A dermoscopic image of a skin lesion.
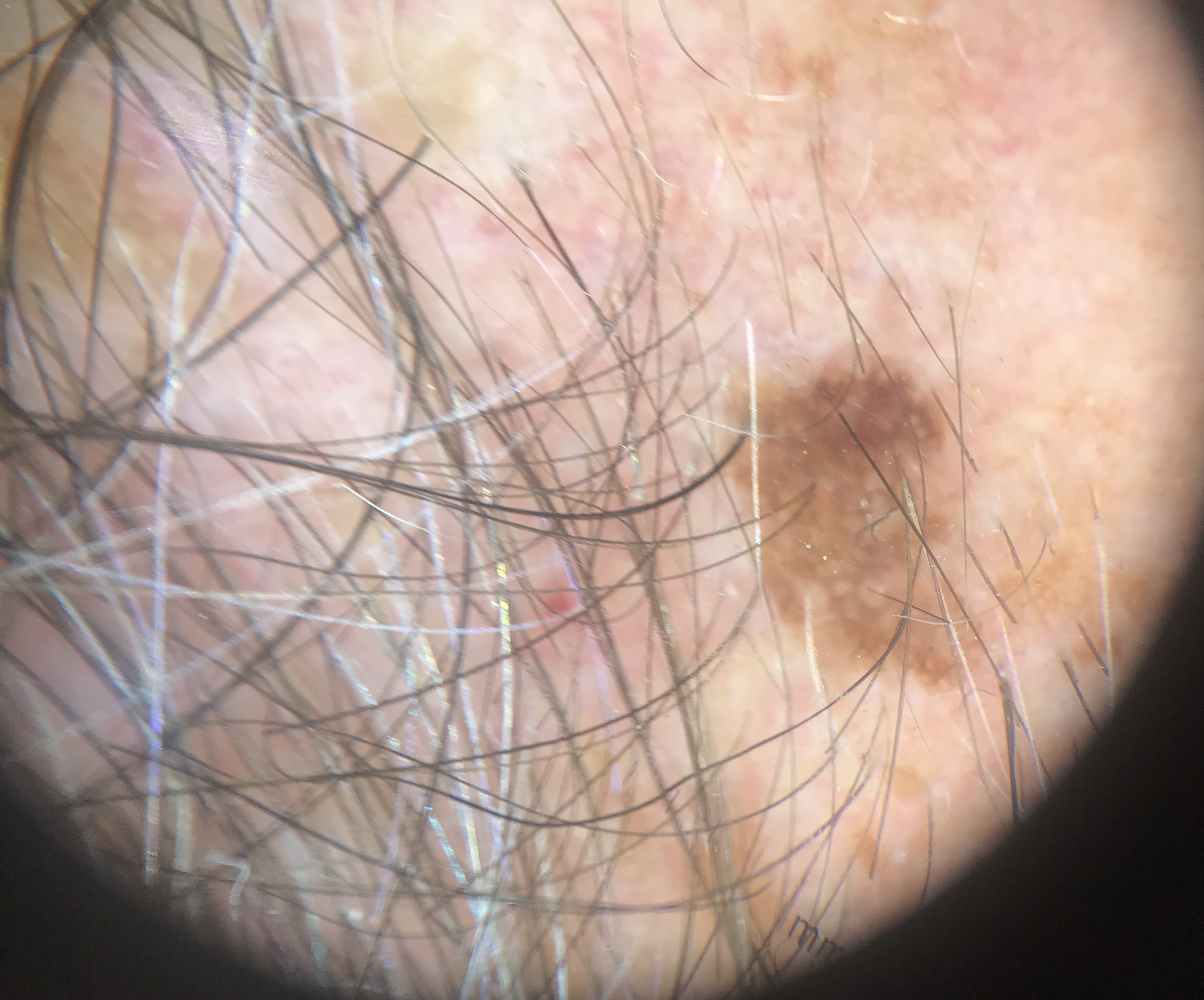This is a keratinocytic lesion. Diagnosed as a benign lesion — a seborrheic keratosis.